This is a close-up image: 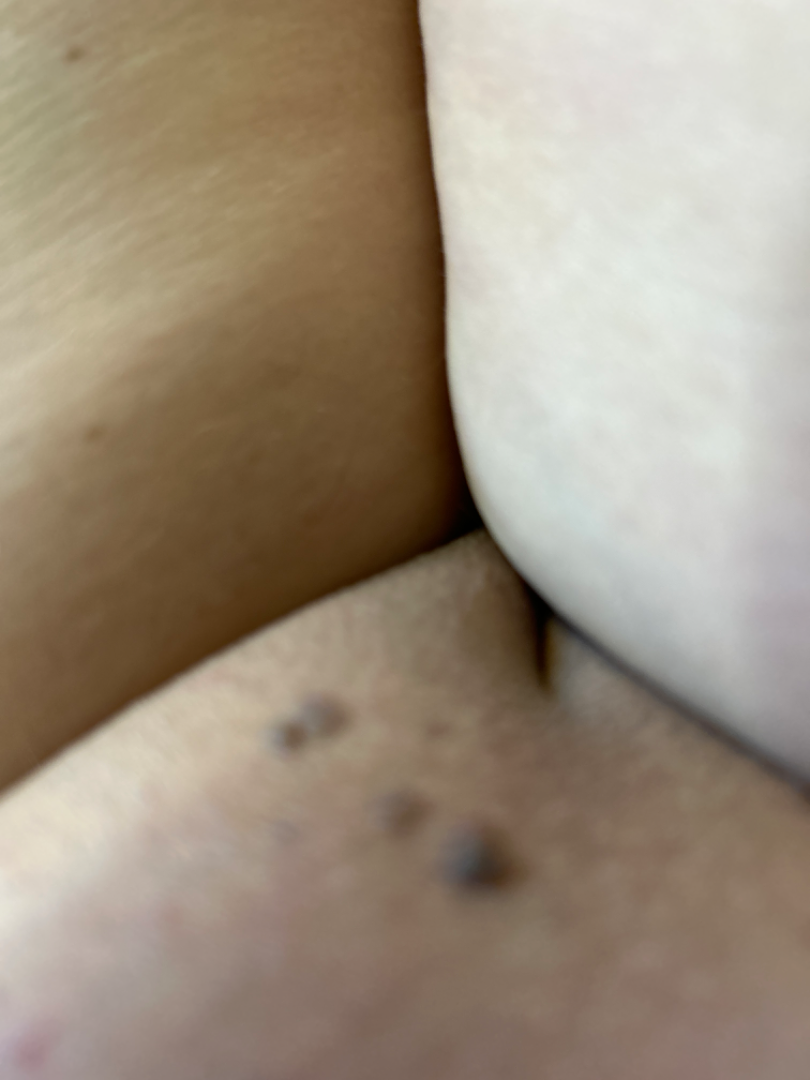| key | value |
|---|---|
| clinical impression | SK/ISK and Condyloma acuminatum were considered with similar weight |